This image was taken at an angle · the subject is a female aged 40–49 · located on the arm and leg: 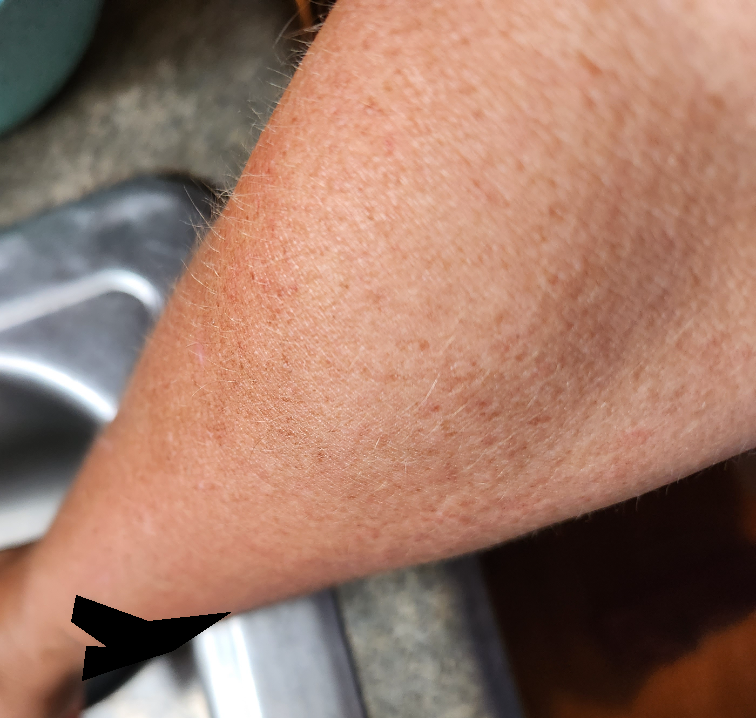Impression: The skin condition could not be confidently assessed from this image. History: The patient reports enlargement and itching. Reported duration is one to four weeks. The patient considered this a rash. Texture is reported as raised or bumpy. No relevant systemic symptoms.